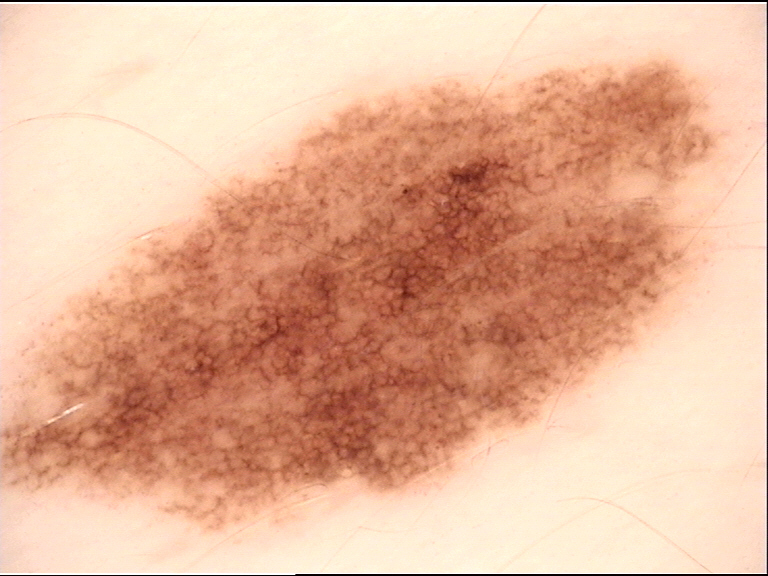{"image": "dermoscopy", "diagnosis": {"name": "dysplastic junctional nevus", "code": "jd", "malignancy": "benign", "super_class": "melanocytic", "confirmation": "expert consensus"}}